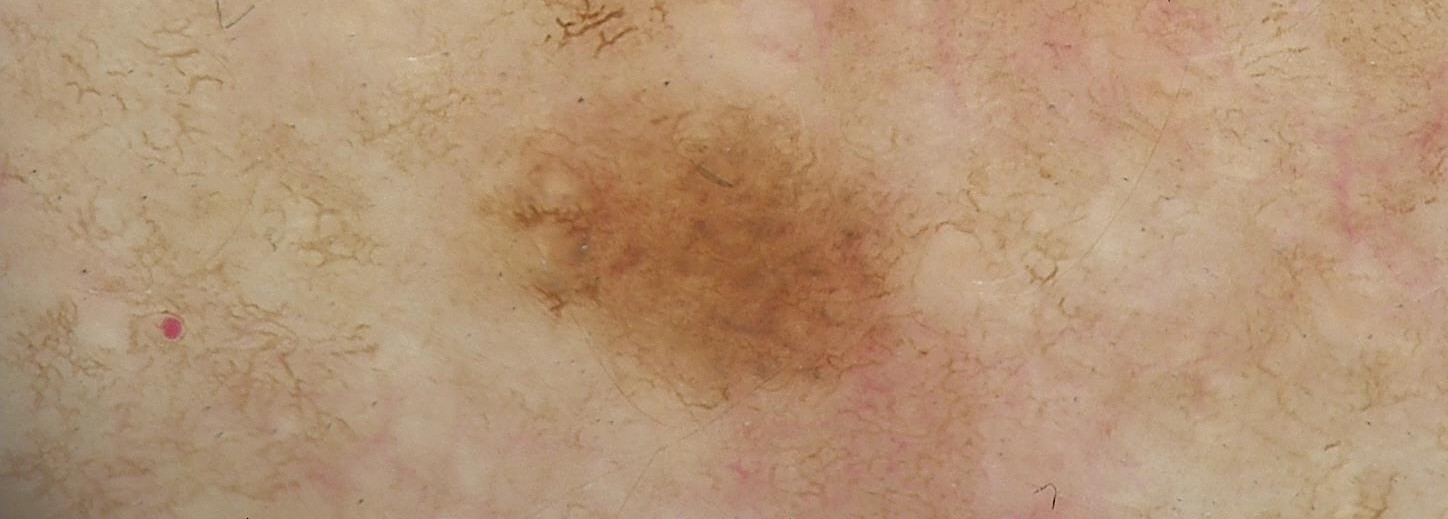A dermatoscopic image of a skin lesion. The diagnostic label was a benign lesion — a dysplastic junctional nevus.